A close-up photograph; the contributor is a female aged 40–49; the lesion involves the palm — 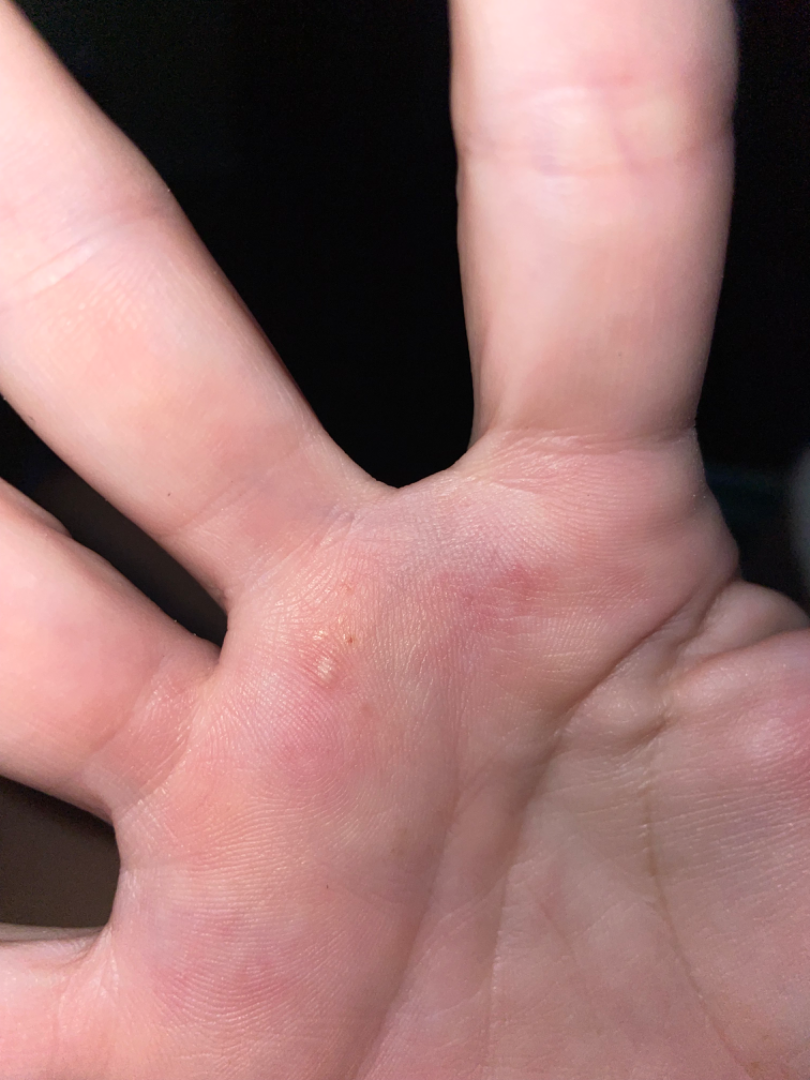One reviewing dermatologist: the impression was split between Insect Bite and Verruca vulgaris; a more distant consideration is Eczema.